The affected area is the back of the torso; the patient is male; this image was taken at a distance:
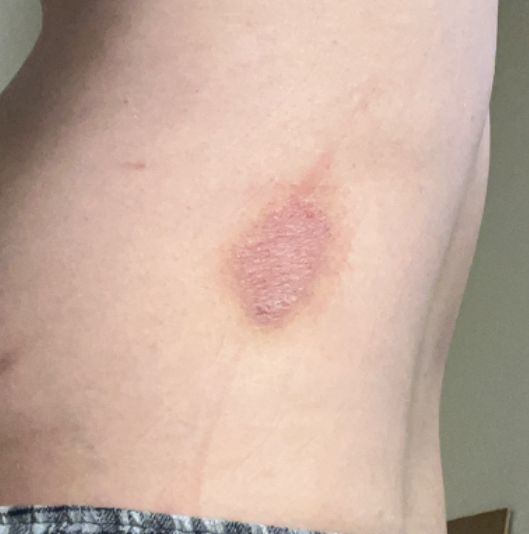The skin findings could not be characterized from the image.
The lesion is described as rough or flaky.
The patient considered this a rash.
The patient indicates the condition has been present for more than one year.
Reported lesion symptoms include itching.